The photograph is a close-up of the affected area:
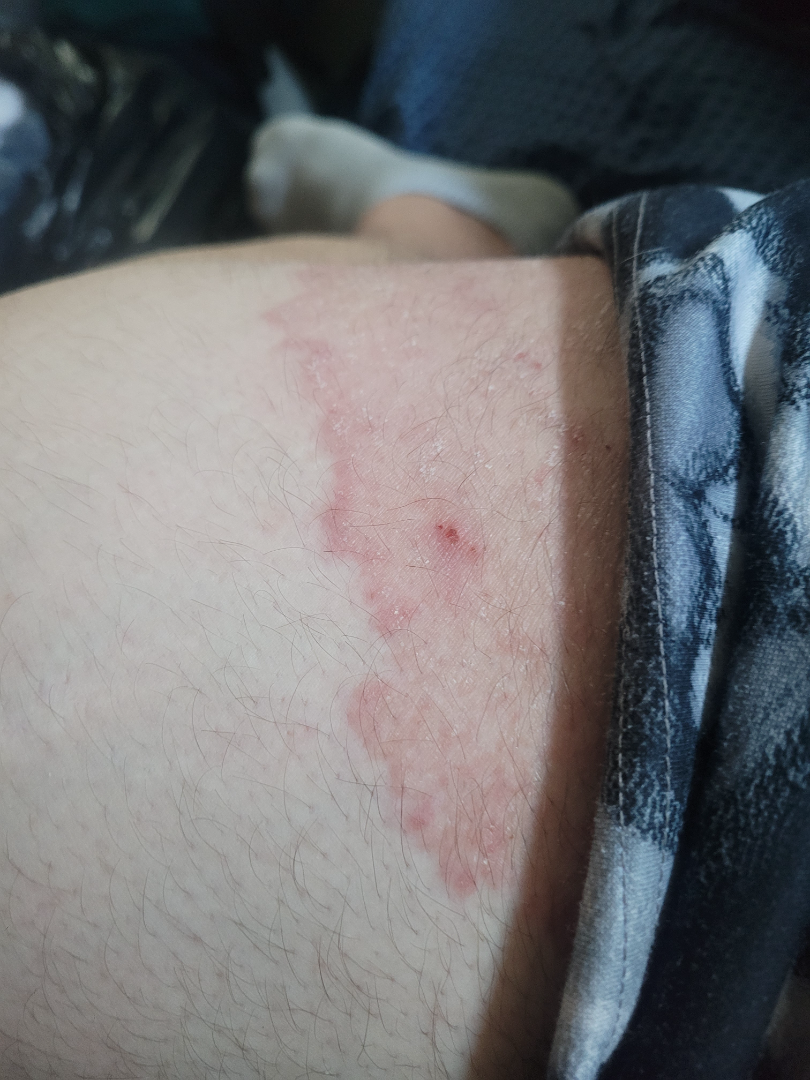Q: What is the differential diagnosis?
A: consistent with Tinea